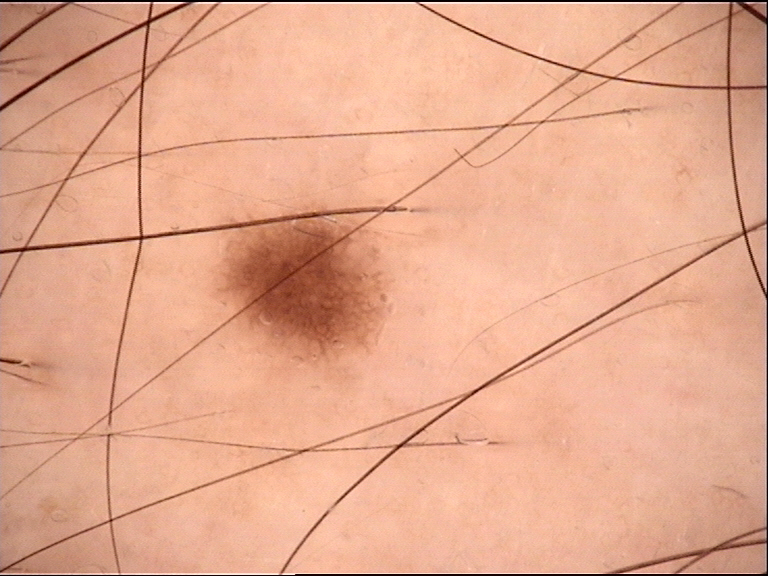class: dysplastic junctional nevus (expert consensus).